A male subject in their late 50s · recorded as Fitzpatrick skin type II · by history, pesticide exposure, prior skin cancer (patient or family), and alcohol use · a clinical close-up photograph of a skin lesion: 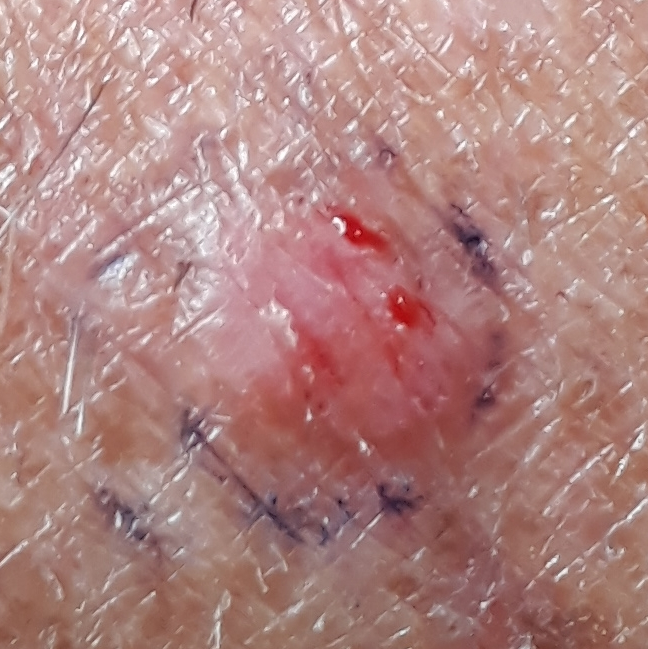size — 5 × 5 mm
patient-reported symptoms — elevation, pain, itching, bleeding
pathology — basal cell carcinoma (biopsy-proven)